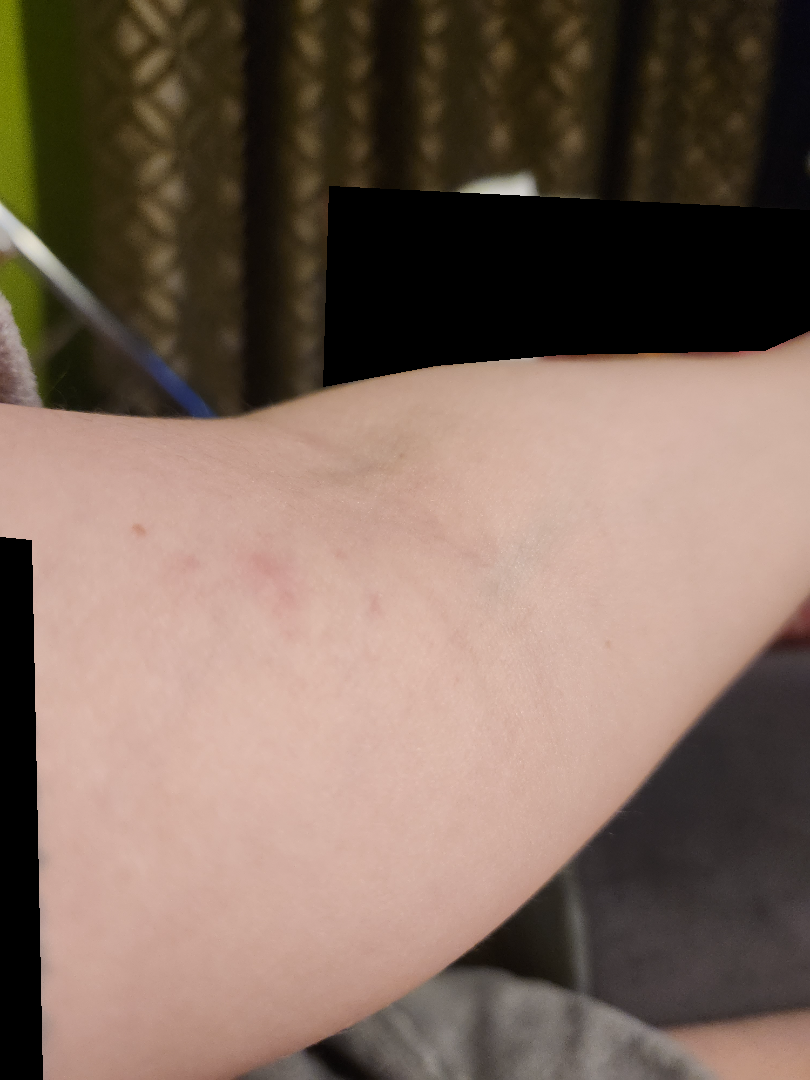Notes:
* lesion texture: raised or bumpy
* anatomic site: arm
* shot type: at an angle
* contributor: female
* history: about one day
* patient's own categorization: a rash
* assessment: the impression on review was Eczema